A dermoscopic image of a skin lesion, the subject is a male roughly 15 years of age.
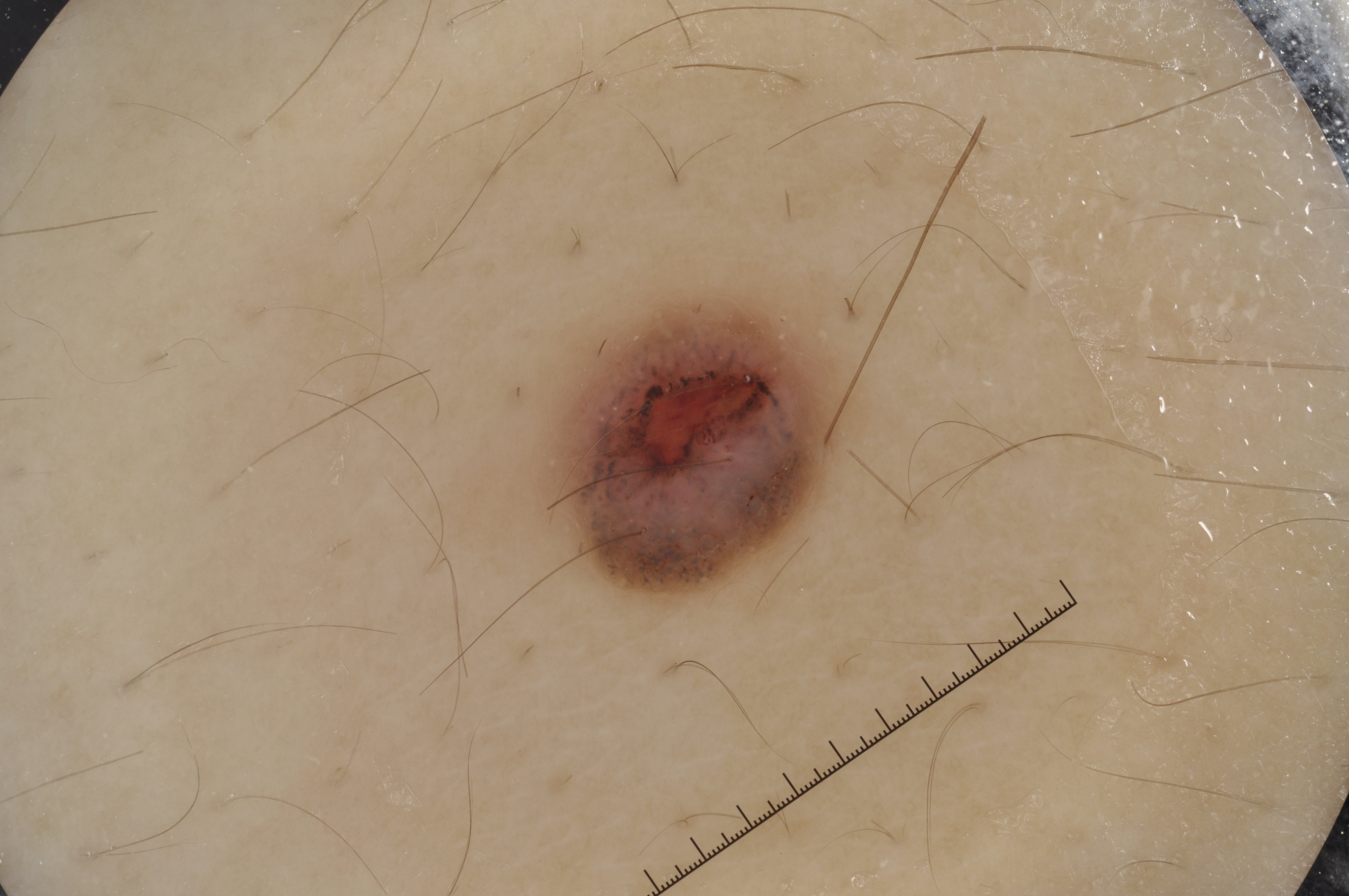– dermoscopic pattern — milia-like cysts
– size — small
– lesion location — 538, 287, 864, 602
– assessment — a melanocytic nevus, a benign lesion